A male subject 83 years of age · a clinical photograph of a skin lesion:
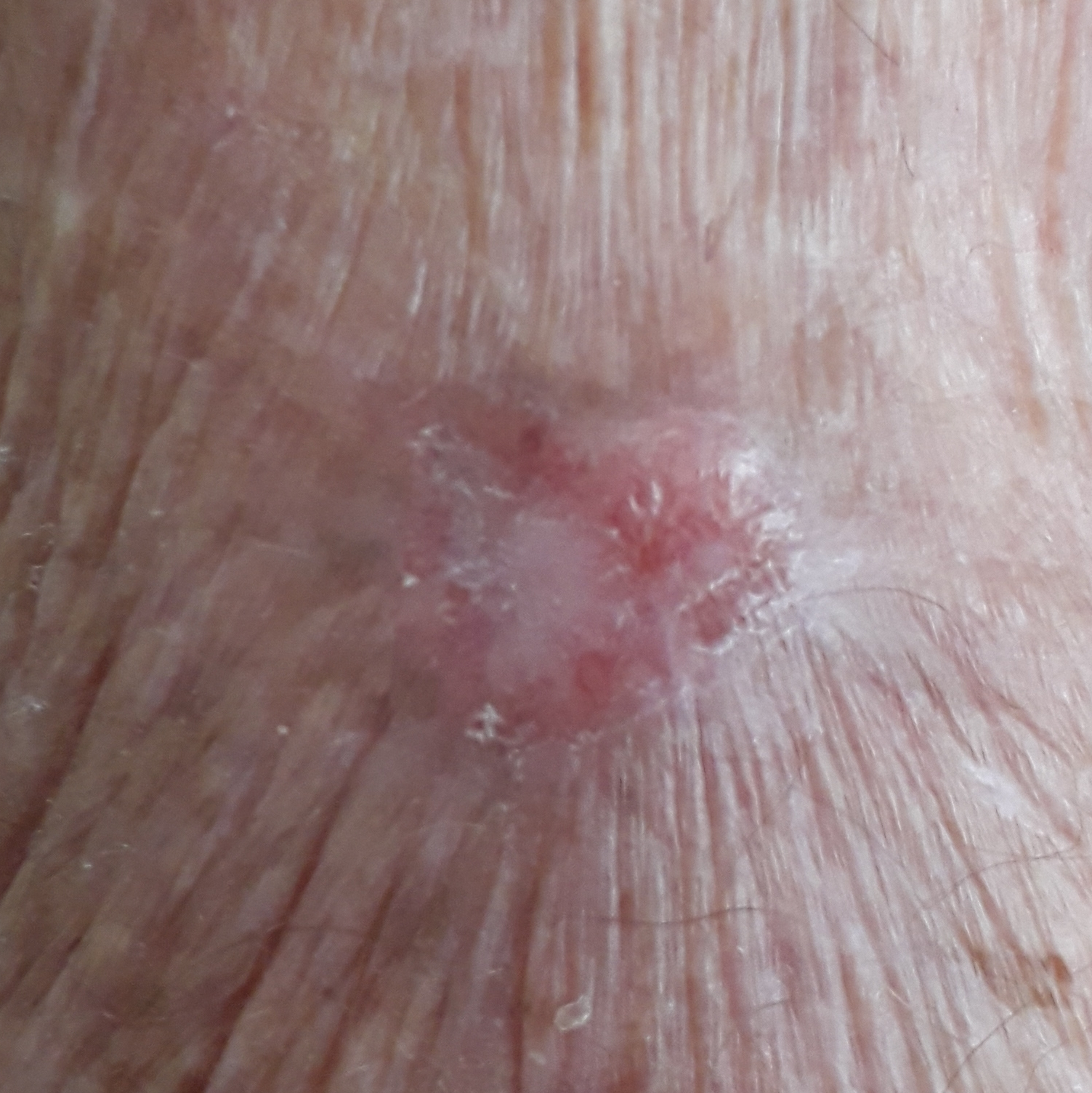Q: What is the anatomic site?
A: a forearm
Q: What symptoms does the patient report?
A: itching, growth / no pain, no bleeding
Q: What is the diagnosis?
A: basal cell carcinoma (biopsy-proven)